Located on the leg · the subject is 50–59, male · the photograph was taken at an angle: 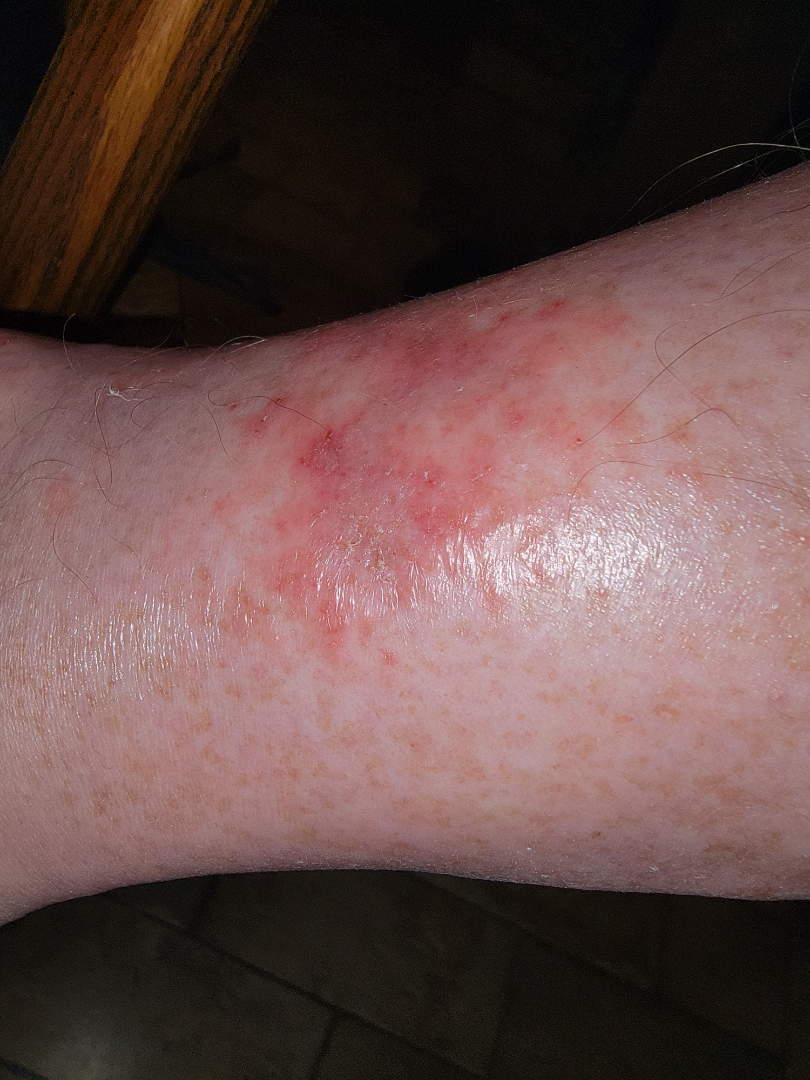<dermatology_case>
  <differential>
    <leading>Stasis Dermatitis</leading>
    <considered>Irritant Contact Dermatitis, Eczema</considered>
    <unlikely>Allergic Contact Dermatitis</unlikely>
  </differential>
</dermatology_case>